A male subject aged 68-72, a dermatoscopic image of a skin lesion: 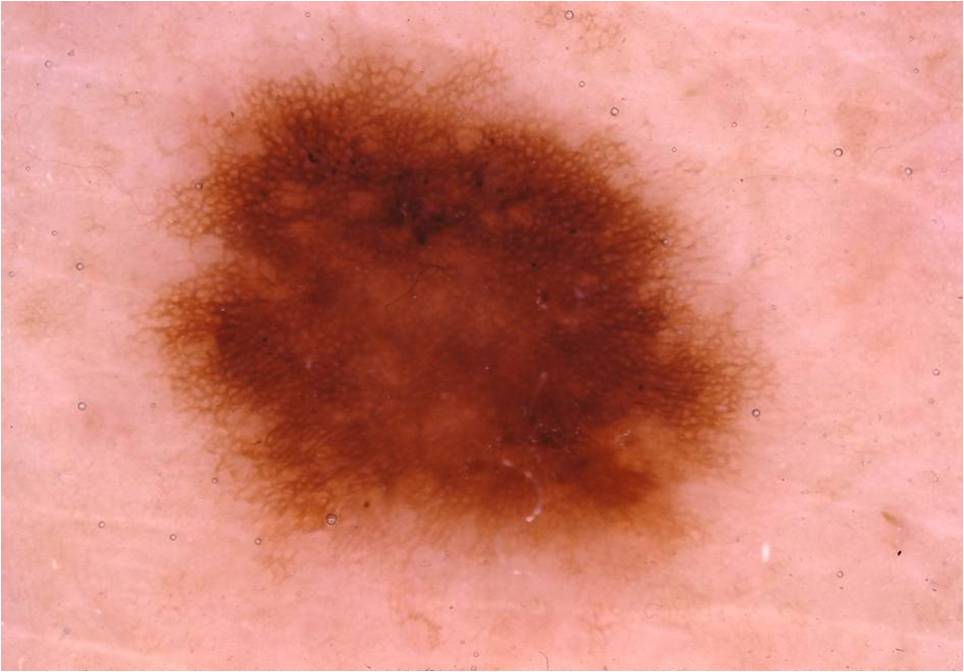<case>
  <dermoscopic_features>
    <present>pigment network, globules</present>
    <absent>milia-like cysts, negative network, streaks</absent>
  </dermoscopic_features>
  <lesion_location>
    <bbox_xyxy>125, 37, 799, 618</bbox_xyxy>
  </lesion_location>
  <diagnosis>
    <name>melanocytic nevus</name>
    <malignancy>benign</malignancy>
    <lineage>melanocytic</lineage>
    <provenance>clinical</provenance>
  </diagnosis>
</case>